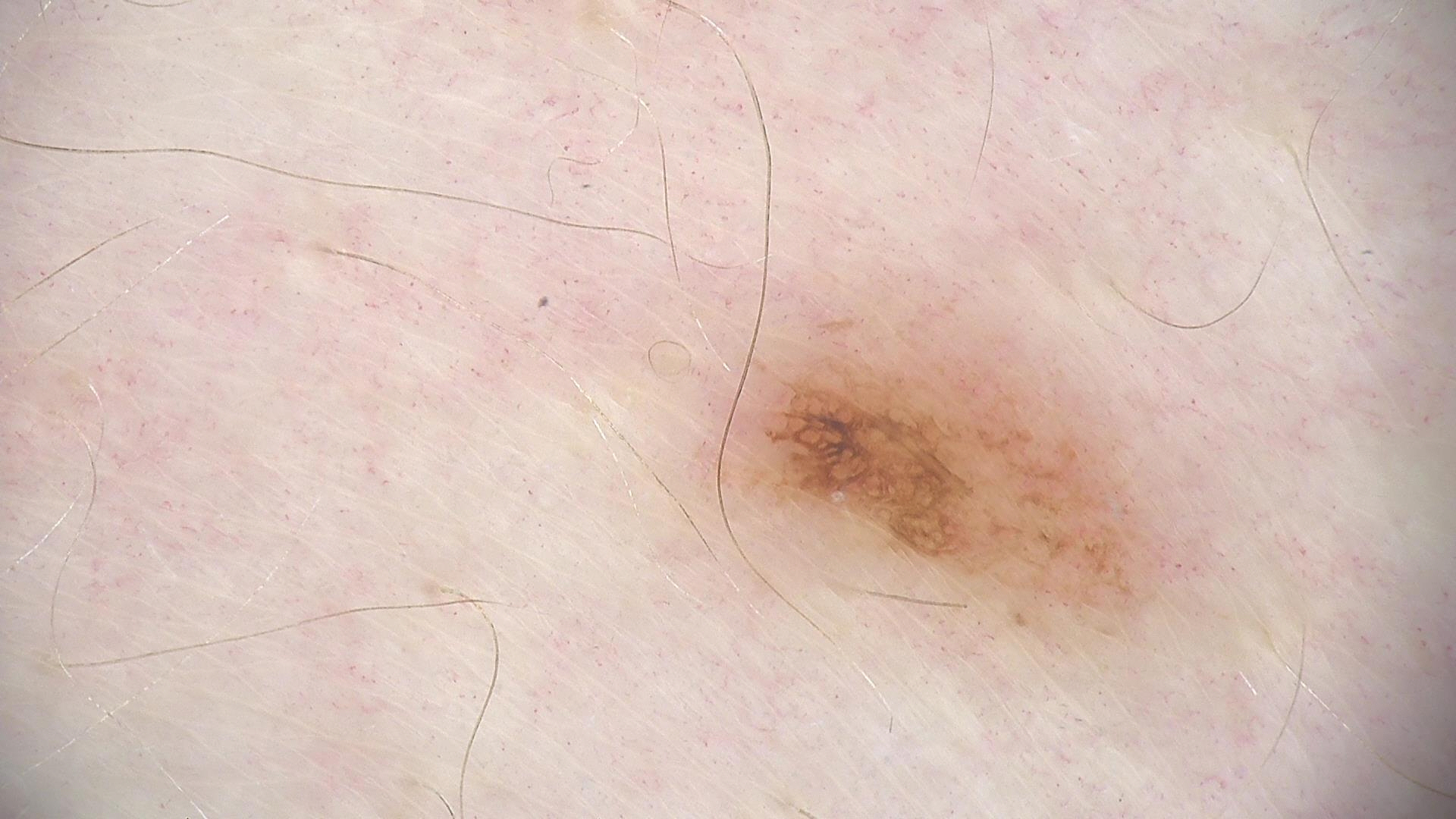Q: What is the diagnosis?
A: compound nevus (expert consensus)